A clinical photograph showing a skin lesion; a subject 49 years of age:
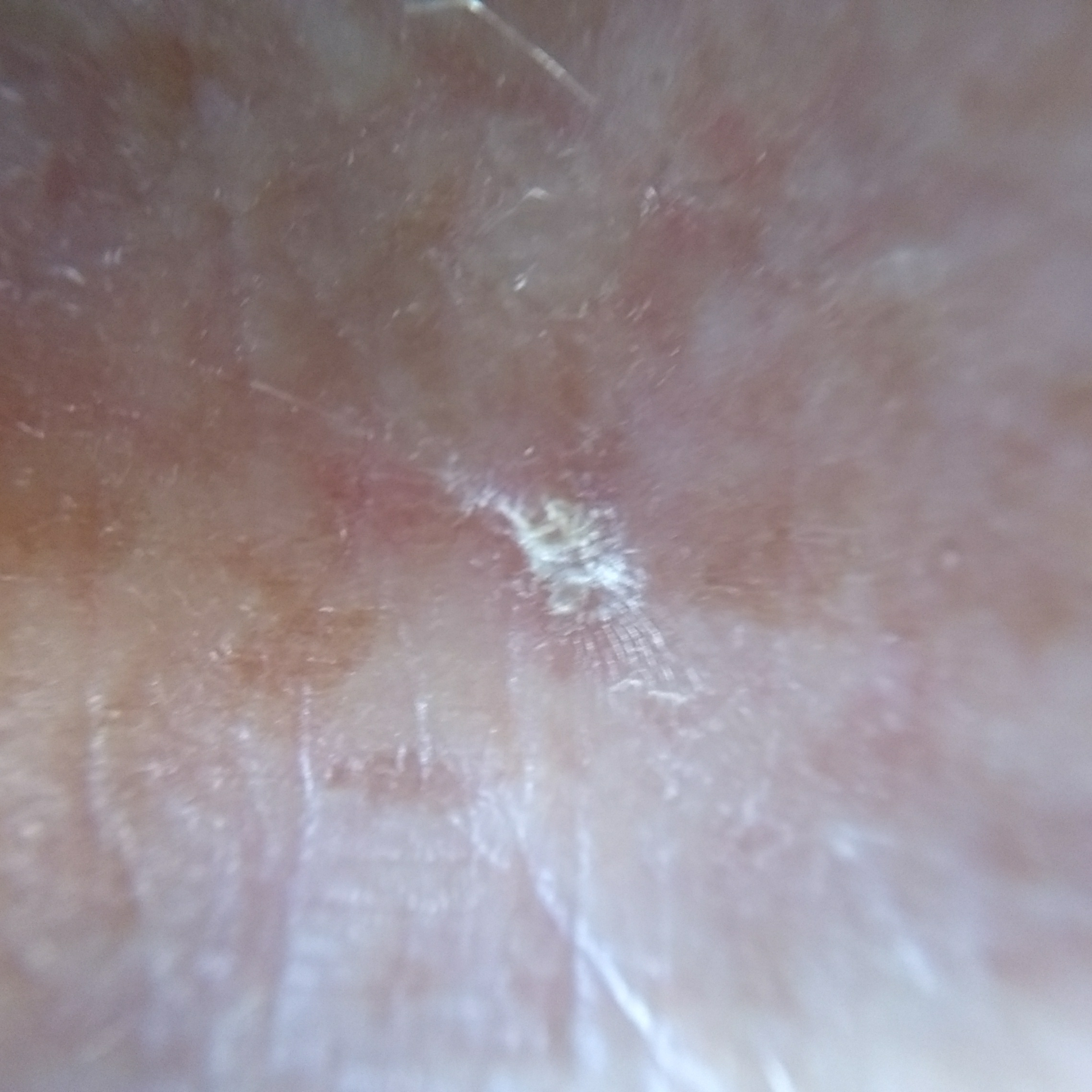Located on a hand. By the patient's account, the lesion itches, but is not elevated. The clinical impression was an actinic keratosis.